A close-up photograph.
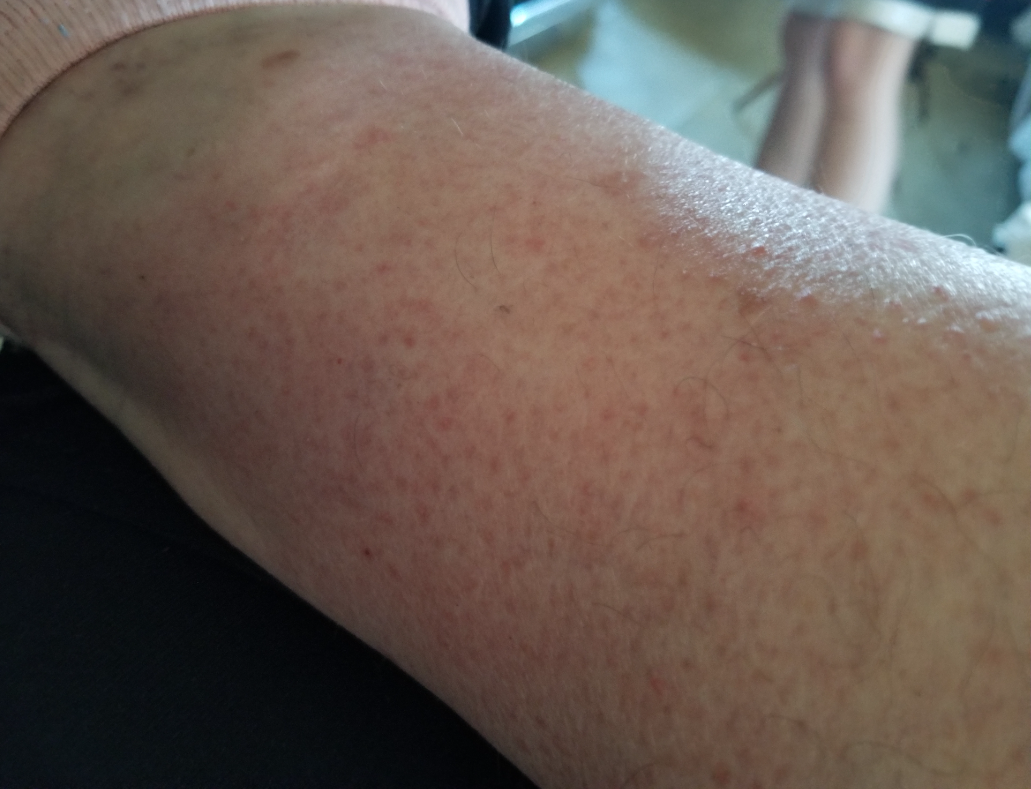{
  "differential": {
    "tied_lead": [
      "Stasis Dermatitis",
      "Eczema",
      "Allergic Contact Dermatitis"
    ]
  }
}